A skin lesion imaged with a dermatoscope:
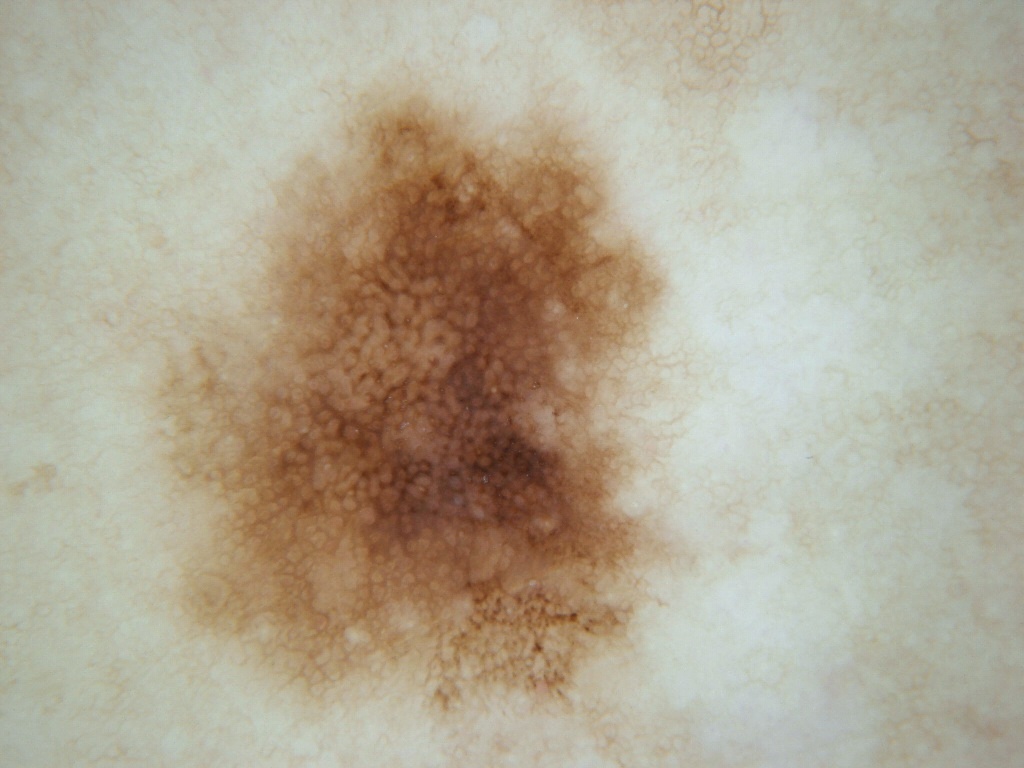Findings:
On dermoscopy, the lesion shows neither streaks nor globules. The lesion's extent is x1=126, y1=44, x2=735, y2=764. The lesion covers approximately 45% of the dermoscopic field.
Assessment:
Consistent with a benign lesion.